A dermatoscopic image of a skin lesion.
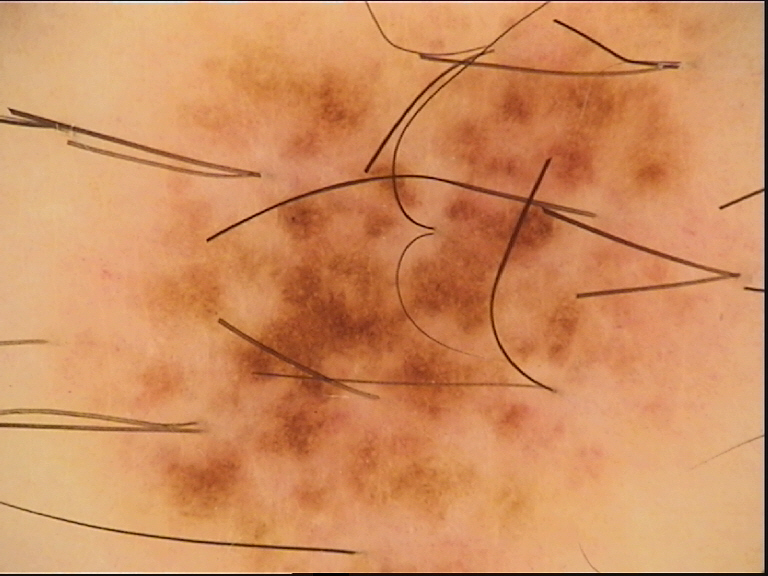Labeled as a benign lesion — a dysplastic junctional nevus.